A dermoscopic view of a skin lesion · a female subject, in their mid- to late 20s.
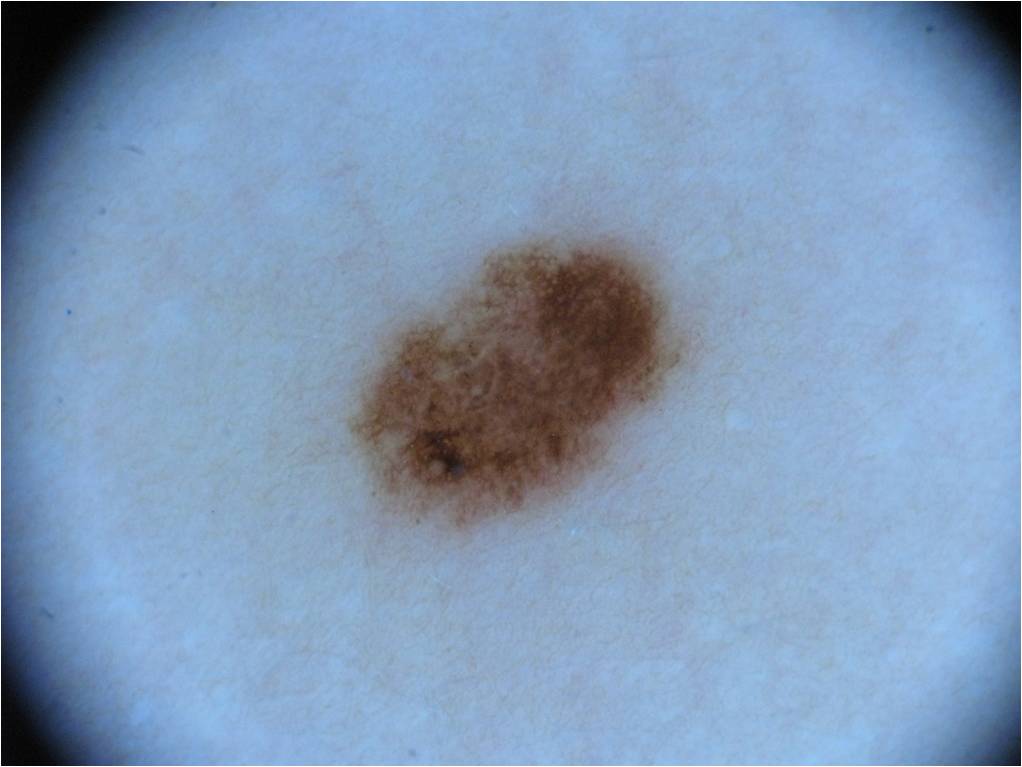{
  "dermoscopic_features": {
    "present": [
      "pigment network",
      "negative network"
    ],
    "absent": [
      "milia-like cysts",
      "globules",
      "streaks"
    ]
  },
  "lesion_location": {
    "bbox_xyxy": [
      347,
      235,
      687,
      530
    ]
  },
  "lesion_extent": {
    "approx_field_fraction_pct": 9
  },
  "diagnosis": {
    "name": "melanocytic nevus",
    "malignancy": "benign",
    "lineage": "melanocytic",
    "provenance": "clinical"
  }
}